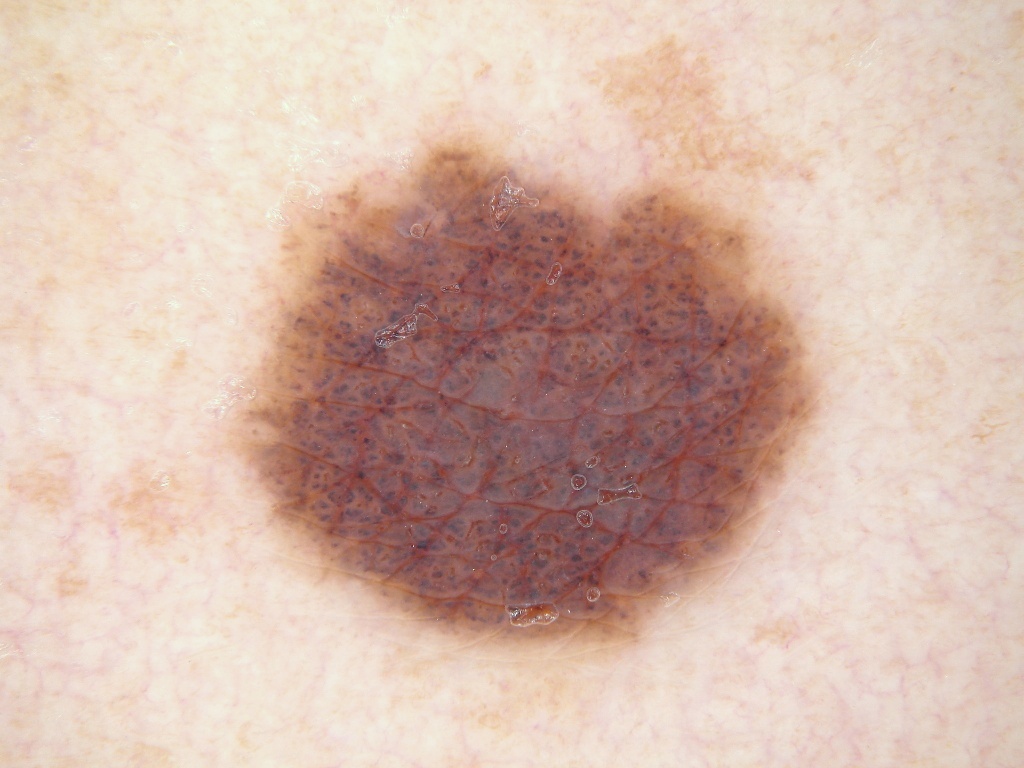Findings:
Dermoscopy of a skin lesion. A female subject aged around 30. The lesion takes up a moderate portion of the field. In (x1, y1, x2, y2) order, the visible lesion spans 232, 136, 820, 652. Dermoscopy demonstrates globules.
Impression:
The diagnostic assessment was a melanocytic nevus, a benign lesion.